A close-up photograph. The patient is 50–59, female. The affected area is the leg. Symptoms reported: itching, burning and darkening. The patient described the issue as a rash. Present for three to twelve months. The lesion is described as flat:
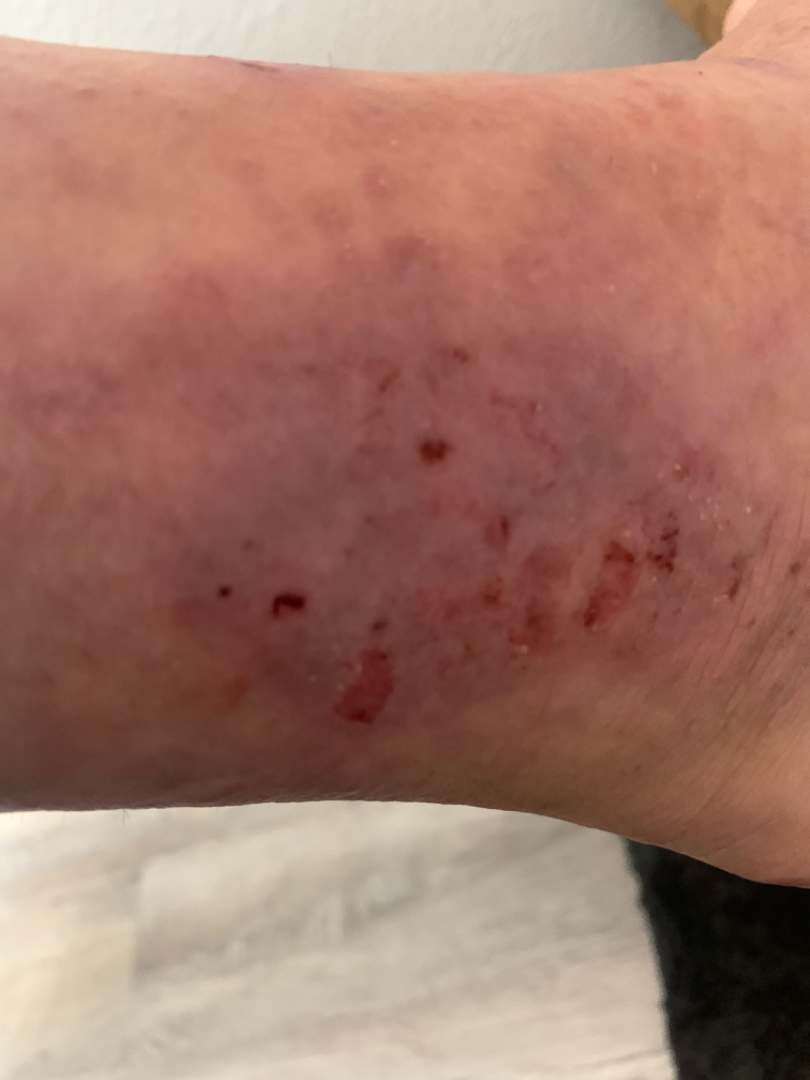Case summary:
* assessment: not assessable